A male patient aged 60 · a clinical photograph showing a skin lesion · history notes pesticide exposure and tobacco use · recorded as Fitzpatrick phototype III.
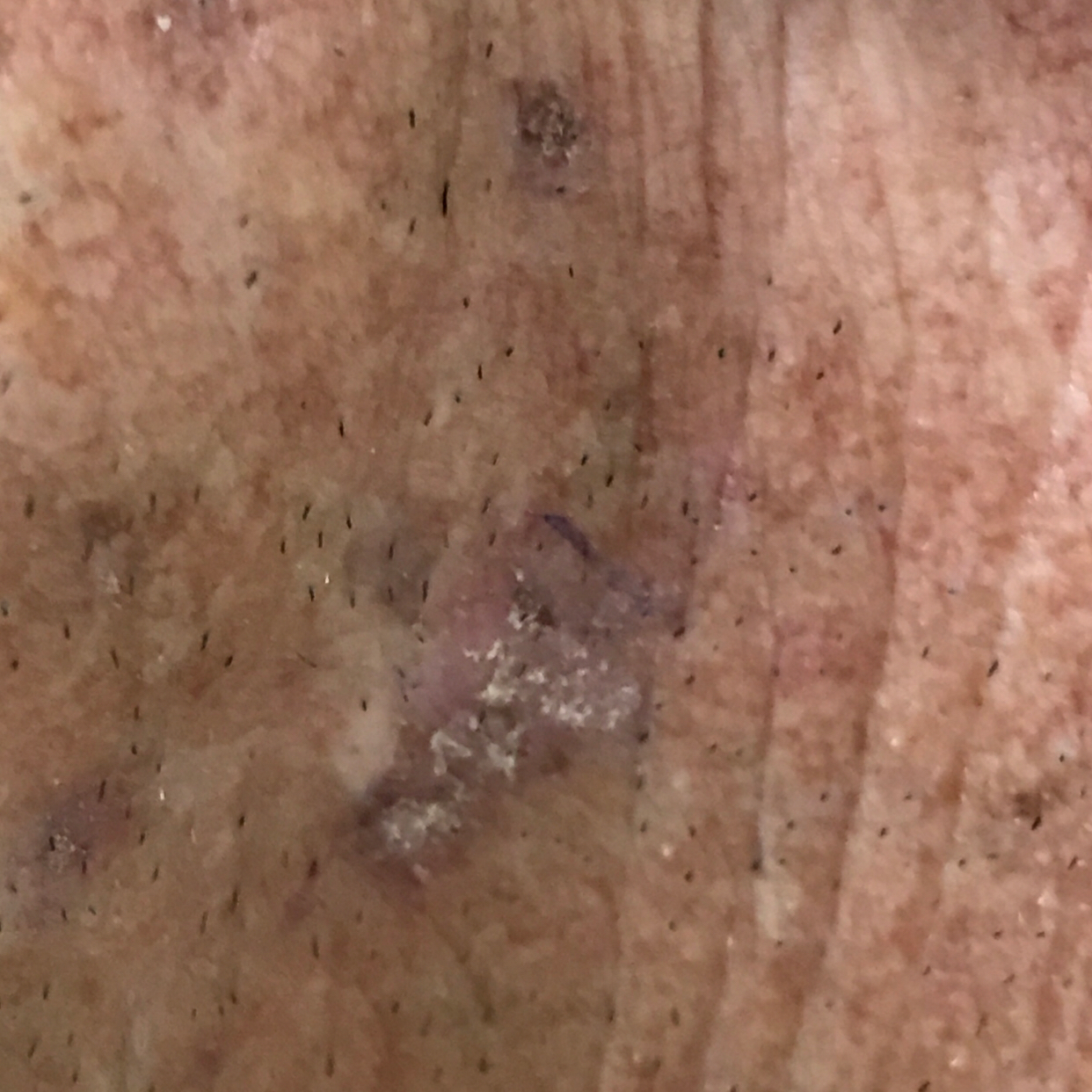Clinical context:
The lesion was found on the face. The lesion measures approximately 20 × 10 mm. By the patient's account, the lesion itches.
Diagnosis:
Biopsy-confirmed as a lesion of indeterminate malignant potential — an actinic keratosis.